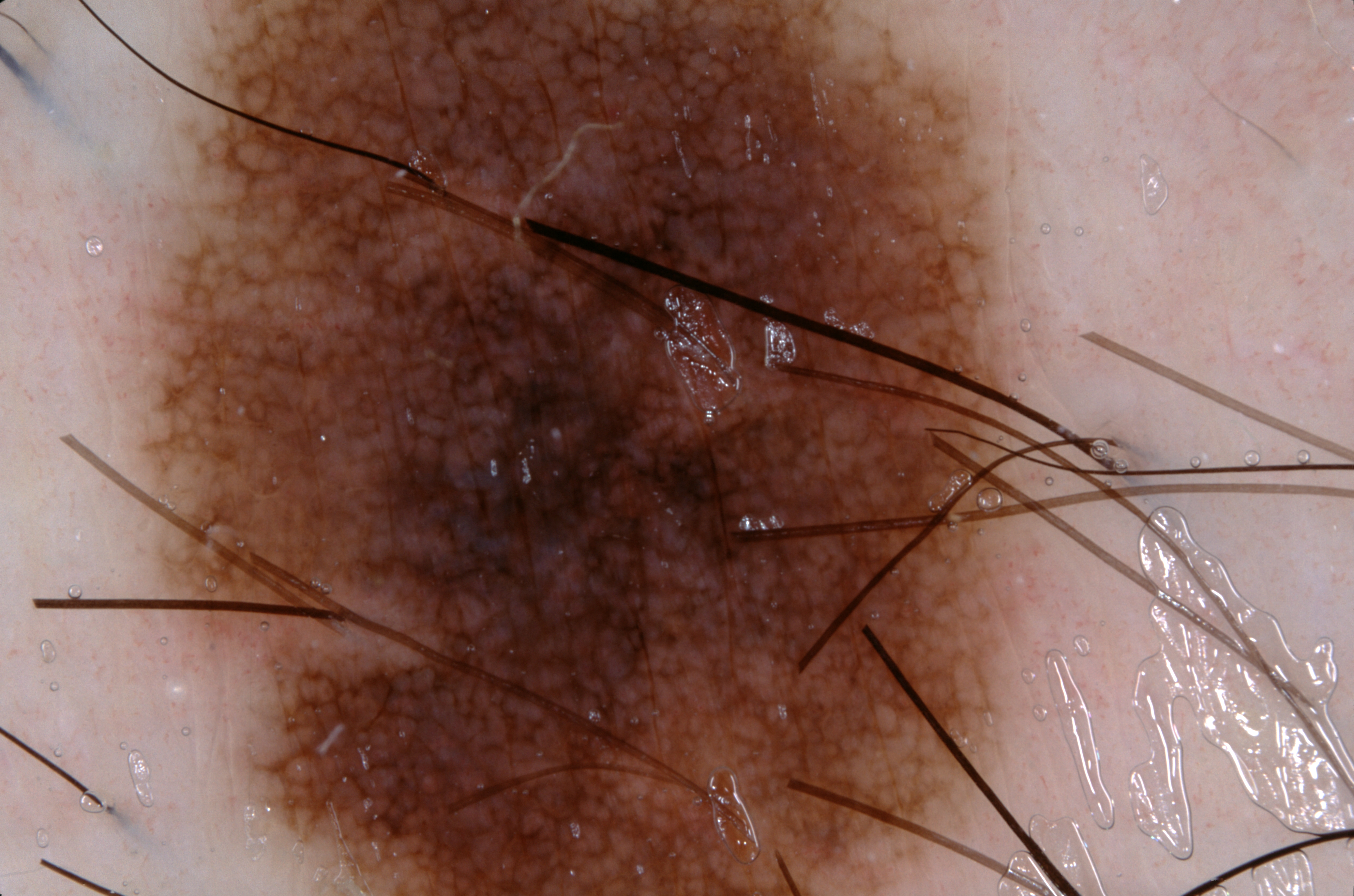Q: What kind of image is this?
A: dermoscopic image
Q: Who is the patient?
A: male, aged approximately 65
Q: What does dermoscopy show?
A: pigment network
Q: Where is the lesion in the image?
A: 93, 1, 1073, 894
Q: Lesion extent?
A: ~65% of the field
Q: What is this lesion?
A: a melanocytic nevus